The leg is involved. Present for less than one week. The photograph was taken at a distance. The patient described the issue as a rash.
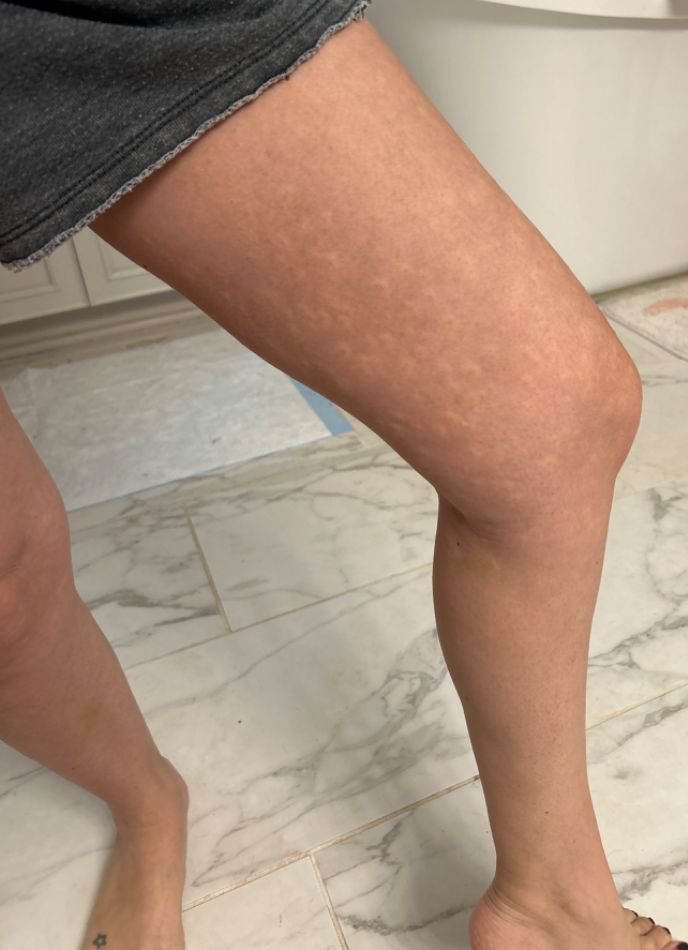The reviewing dermatologist was unable to assign a differential diagnosis from the image.